A smartphone photograph of a skin lesion; a female patient age 62: 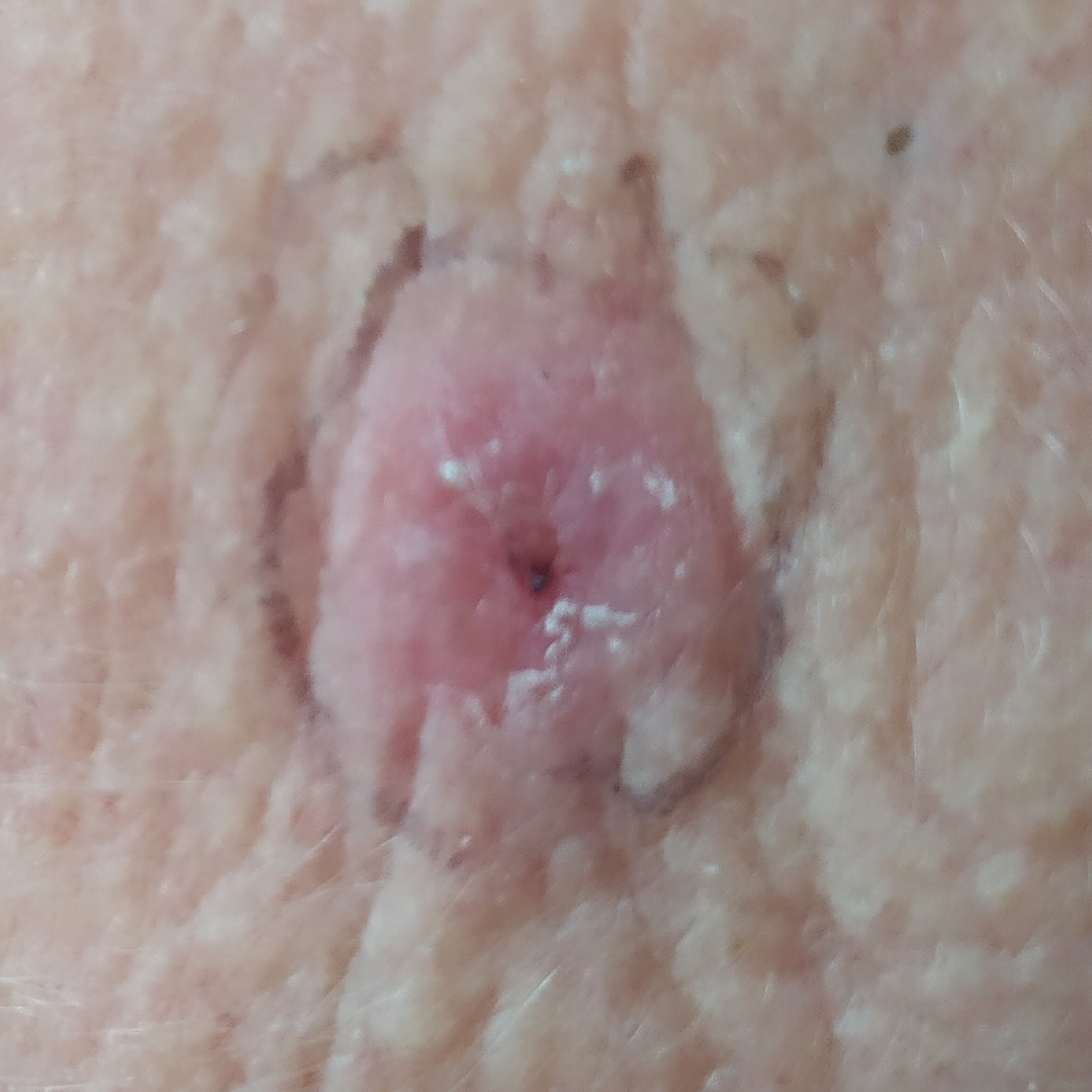| field | value |
|---|---|
| region | the face |
| reported symptoms | itching, elevation, growth |
| pathology | basal cell carcinoma (biopsy-proven) |